Self-categorized by the patient as a rash, the contributor notes the lesion is flat, the affected area is the leg, the photograph is a close-up of the affected area — 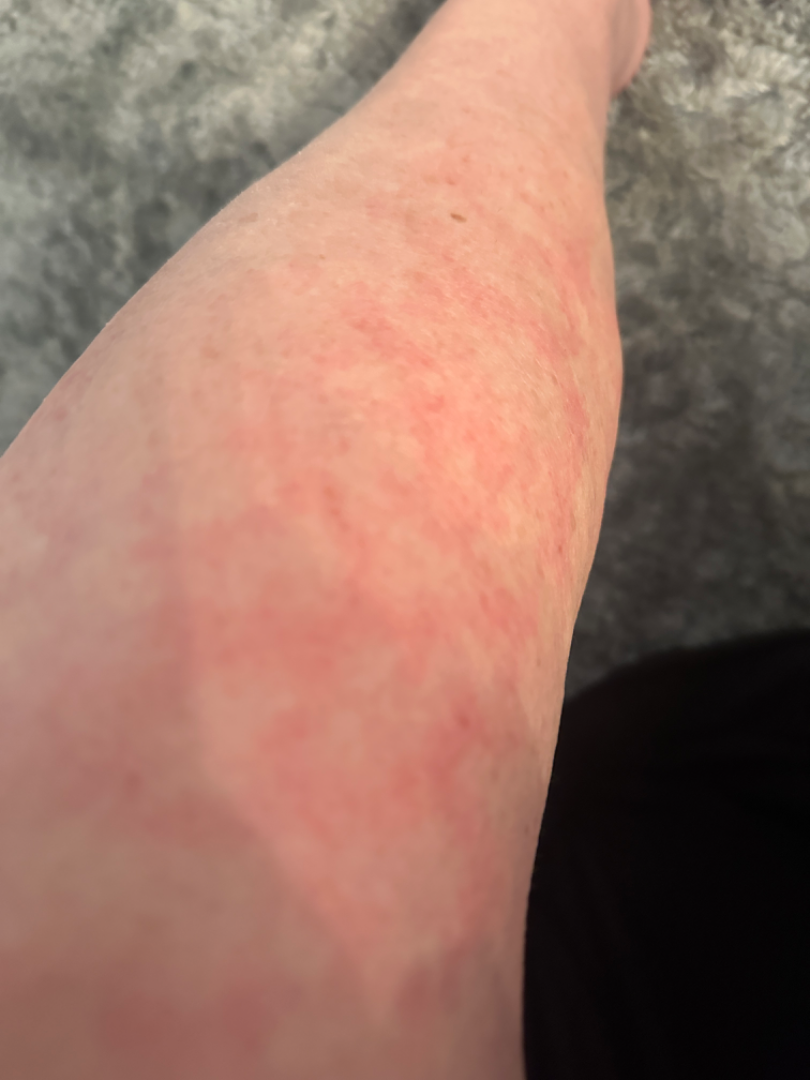assessment: the primary impression is Hypersensitivity; with consideration of Urticaria